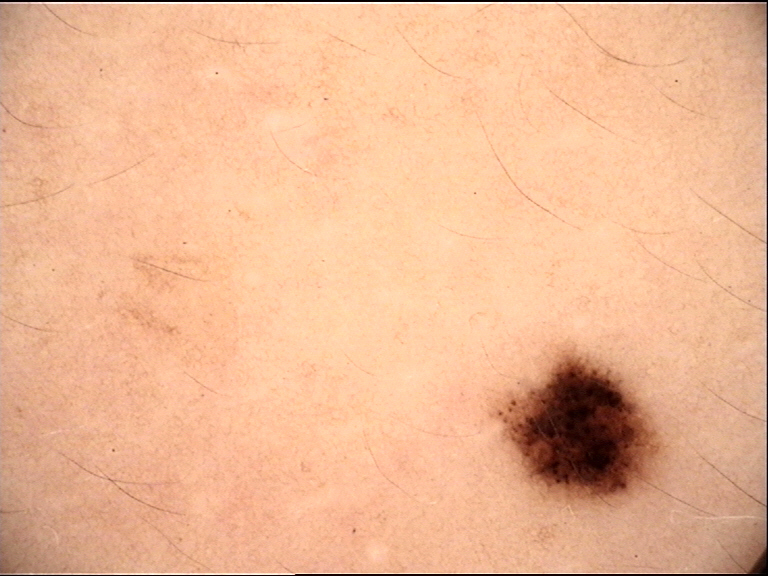Impression:
Classified as a dysplastic junctional nevus.